A dermoscopic close-up of a skin lesion · a male patient aged 23-27.
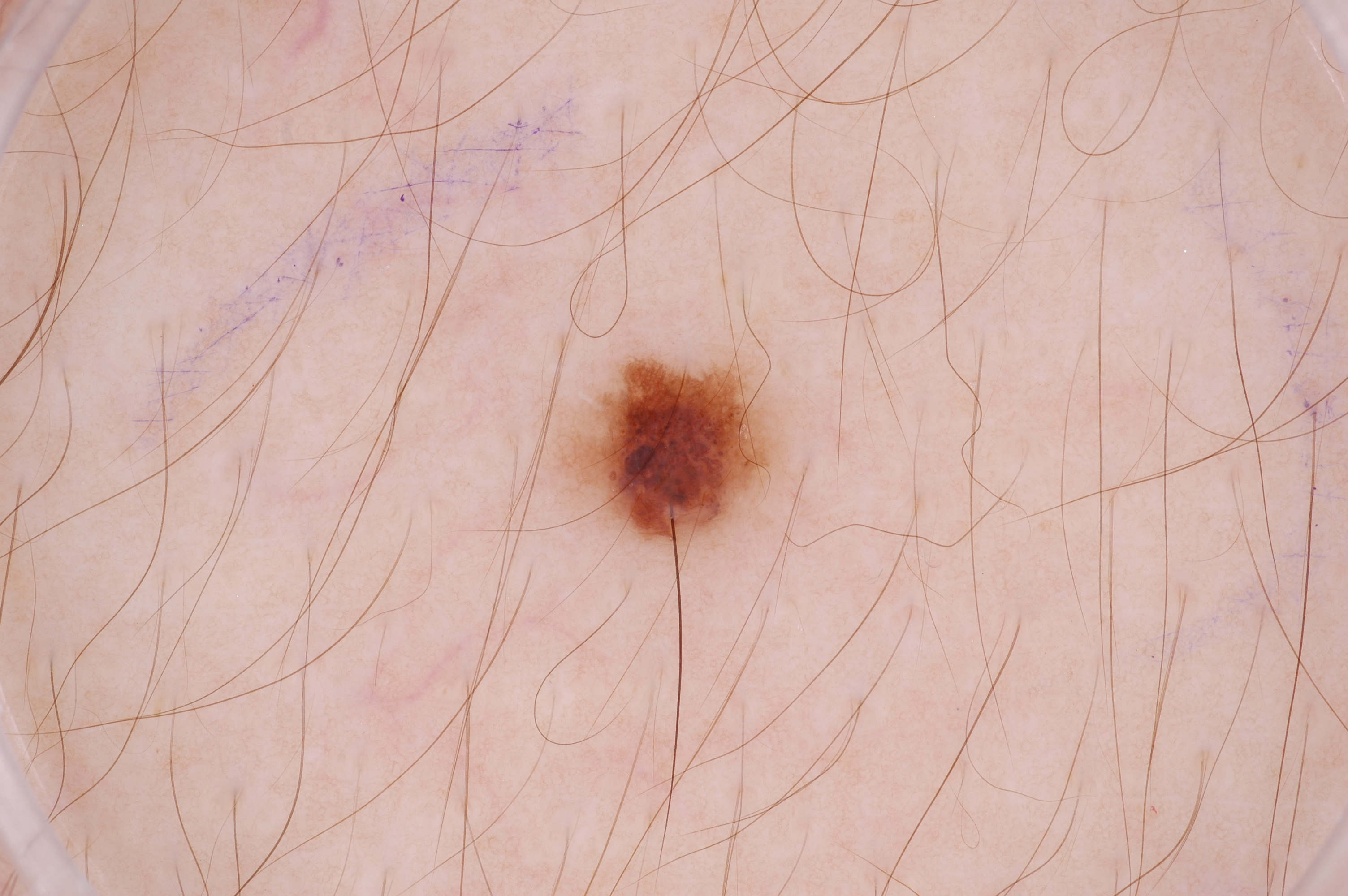  dermoscopic_features:
    present:
      - pigment network
    absent:
      - negative network
      - streaks
      - milia-like cysts
  lesion_location:
    bbox_xyxy:
      - 558
      - 364
      - 779
      - 553
  diagnosis:
    name: melanocytic nevus
    malignancy: benign
    lineage: melanocytic
    provenance: clinical